A male patient in their early 70s · the patient was assessed as Fitzpatrick II · a clinical photograph showing a skin lesion · by history, pesticide exposure and prior malignancy (patient or family).
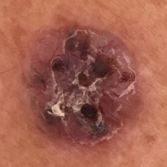location: an arm | lesion diameter: approx. 15 × 13 mm | reported symptoms: itching, bleeding, elevation, growth, pain / no change in appearance | diagnostic label: basal cell carcinoma (biopsy-proven).